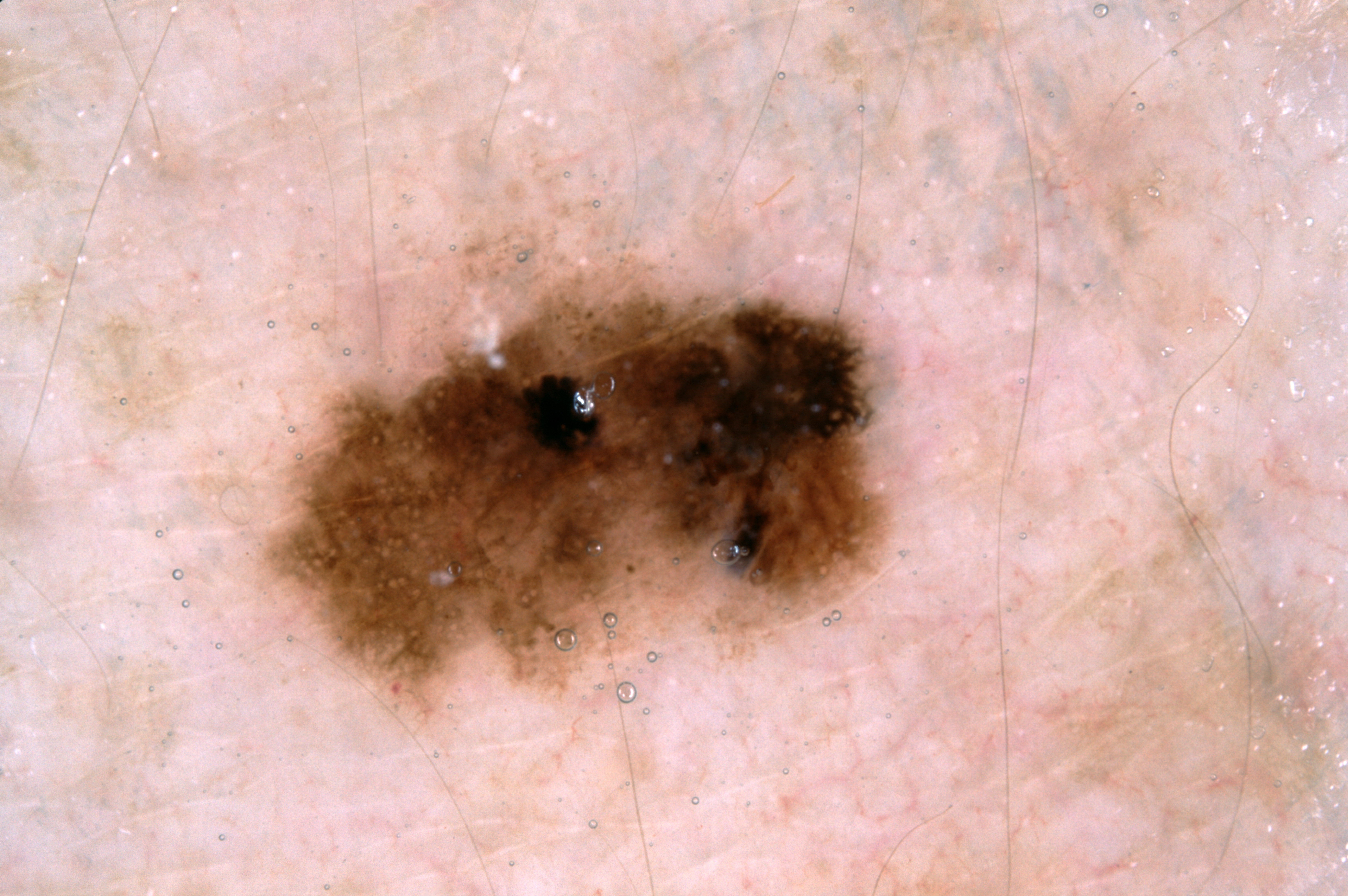Findings: A dermoscopy image of a single skin lesion. The lesion is located at x1=264 y1=265 x2=890 y2=715. On dermoscopy, the lesion shows pigment network. Diagnosis: Histopathological examination showed a melanoma, a malignancy.